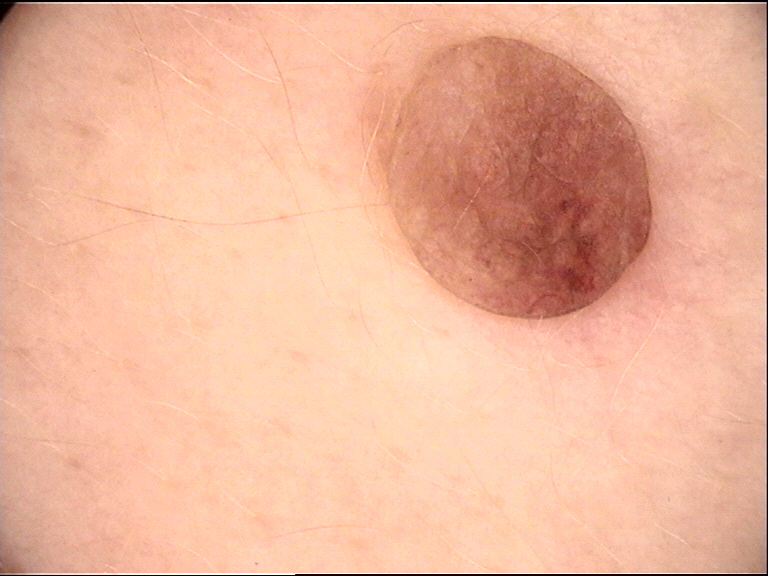Case:
A dermoscopic image of a skin lesion. This is a banal lesion.
Conclusion:
Classified as a dermal nevus.